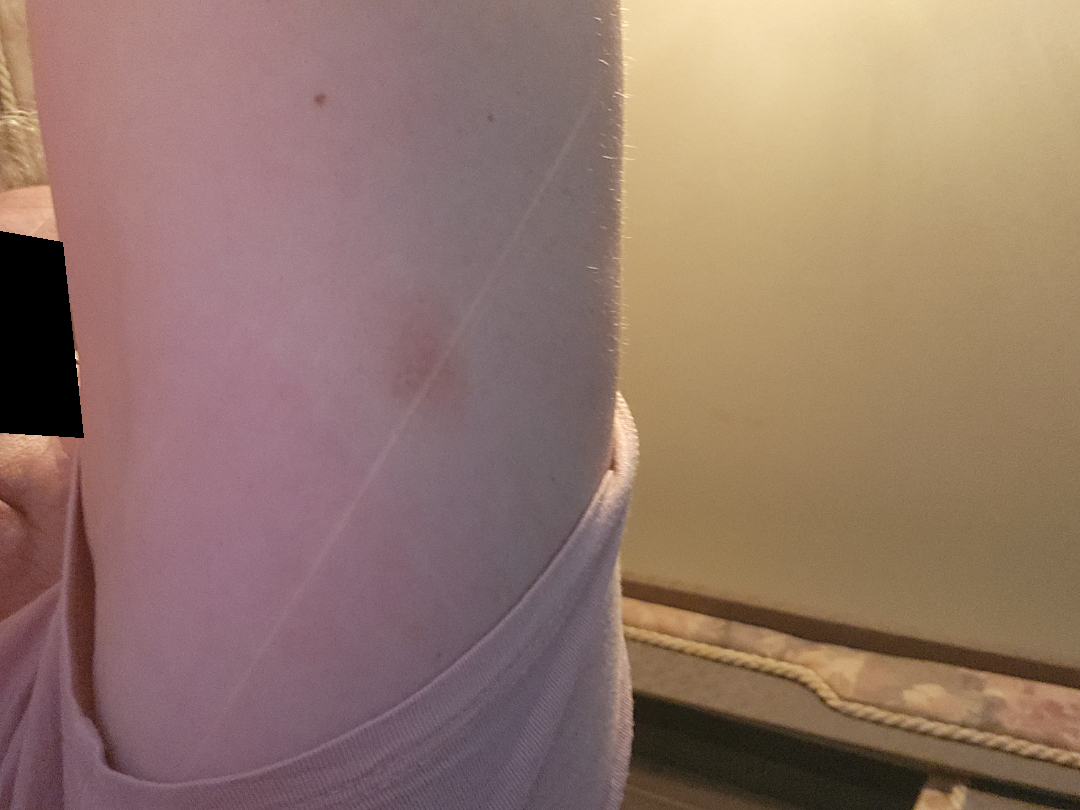assessment = unable to determine | surface texture = flat | location = arm | present for = more than one year | contributor = female, age 50–59 | constitutional symptoms = joint pain, shortness of breath and fatigue | photo taken = at an angle.